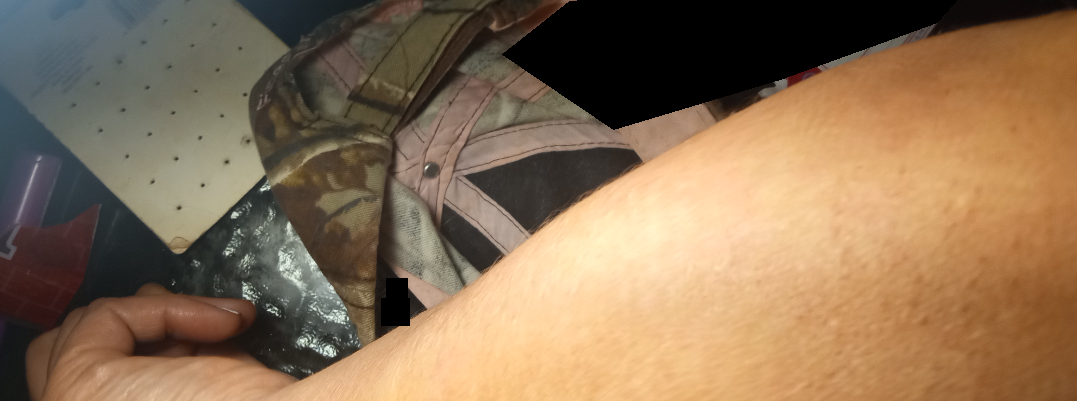Q: What was the assessment?
A: no discernible pathology
Q: Image view?
A: close-up